A clinical photograph showing a skin lesion · a male subject age 65: 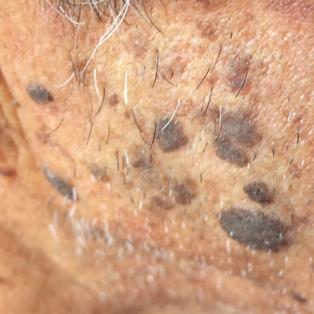patient-reported symptoms: growth, elevation; diagnosis: seborrheic keratosis (clinical consensus).